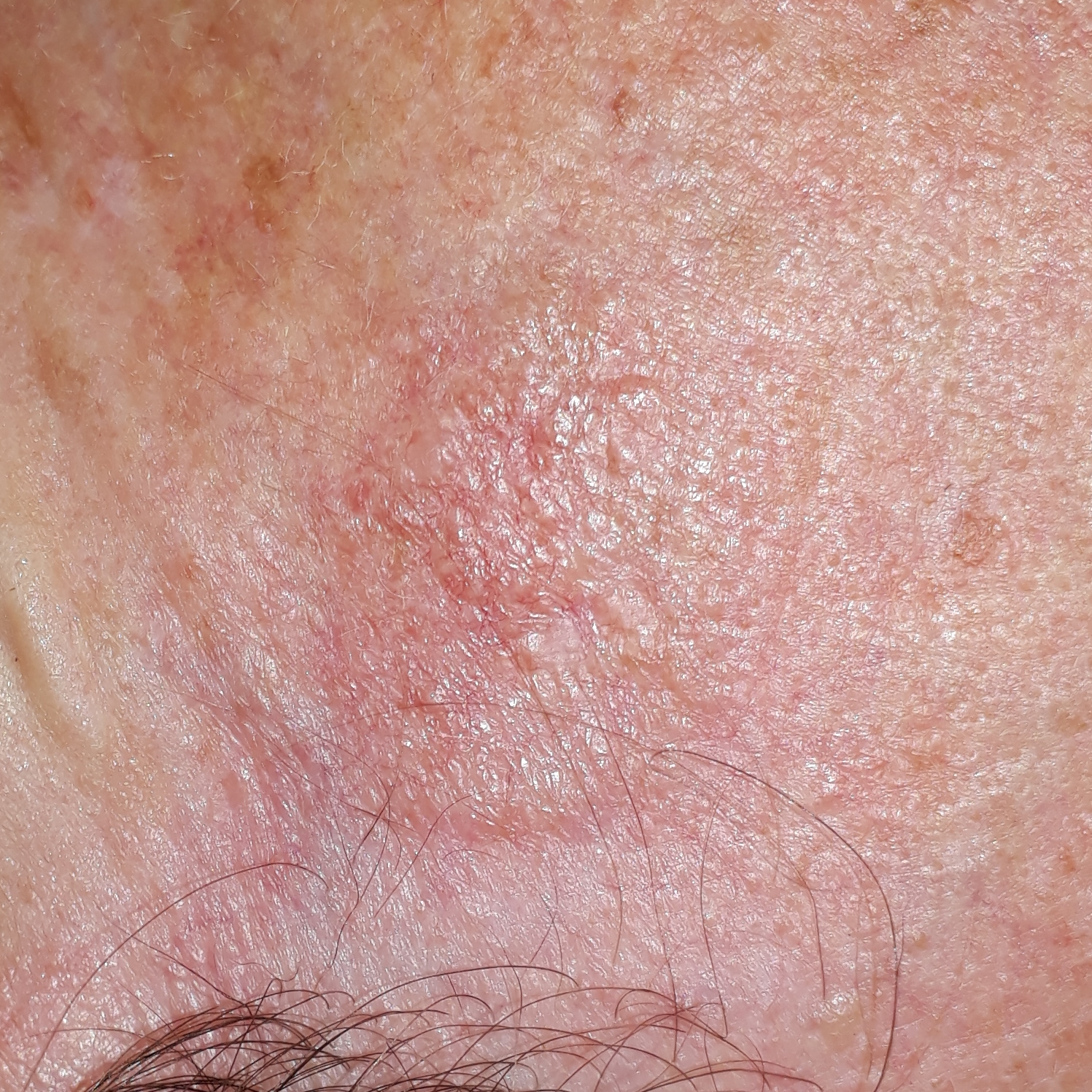Findings: The patient was assessed as Fitzpatrick III. A clinical close-up photograph of a skin lesion. A female subject in their 60s. The lesion involves the face. The patient reports that the lesion itches, but does not hurt and has not bled. Pathology: On biopsy, the diagnosis was a malignant skin lesion — a basal cell carcinoma.